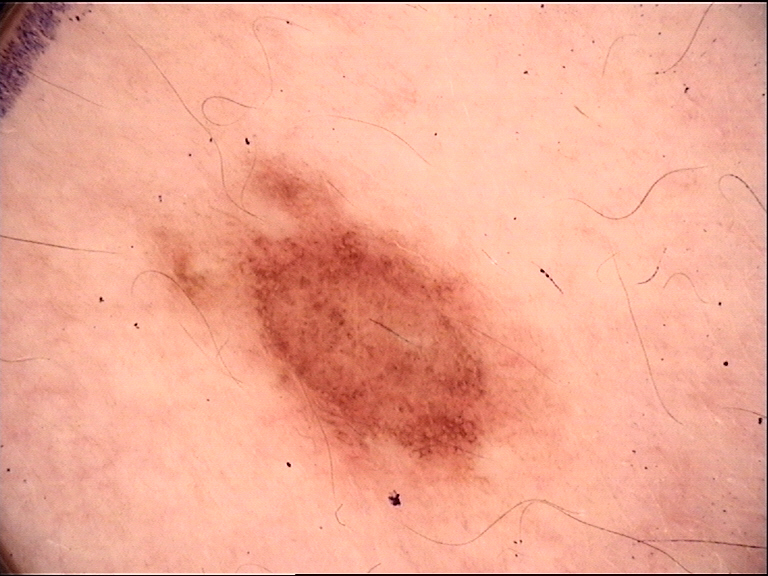class: dysplastic junctional nevus (expert consensus).